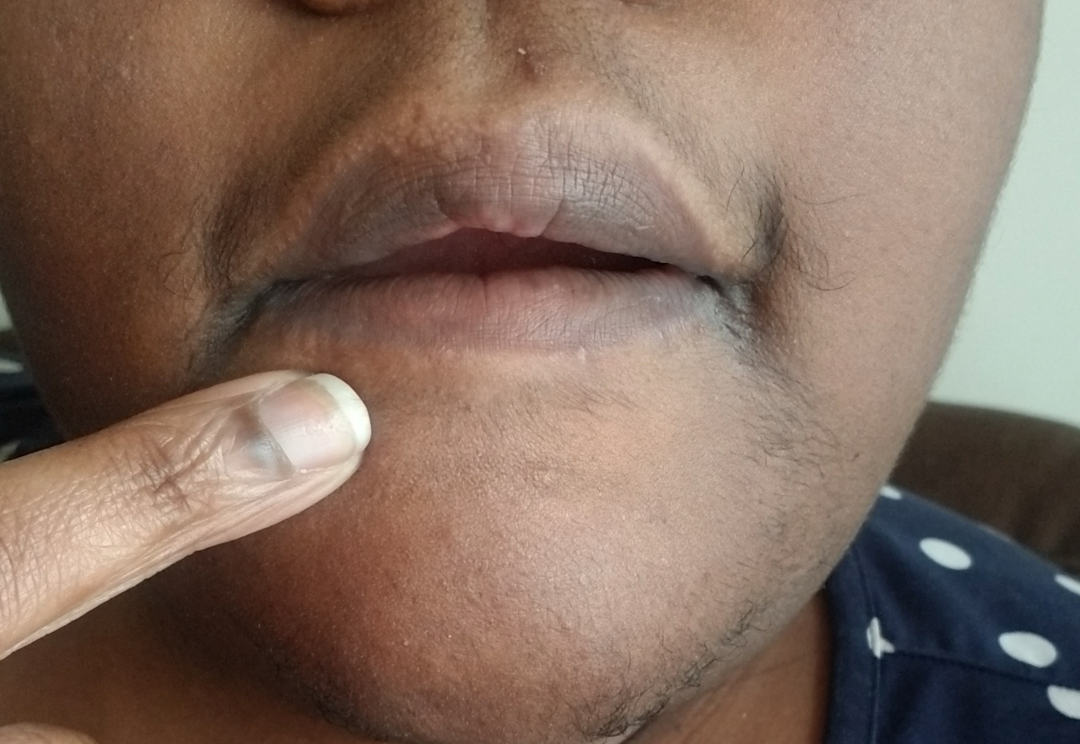<report>
<assessment>none discernible</assessment>
<shot_type>close-up</shot_type>
<patient>female, age 30–39</patient>
</report>